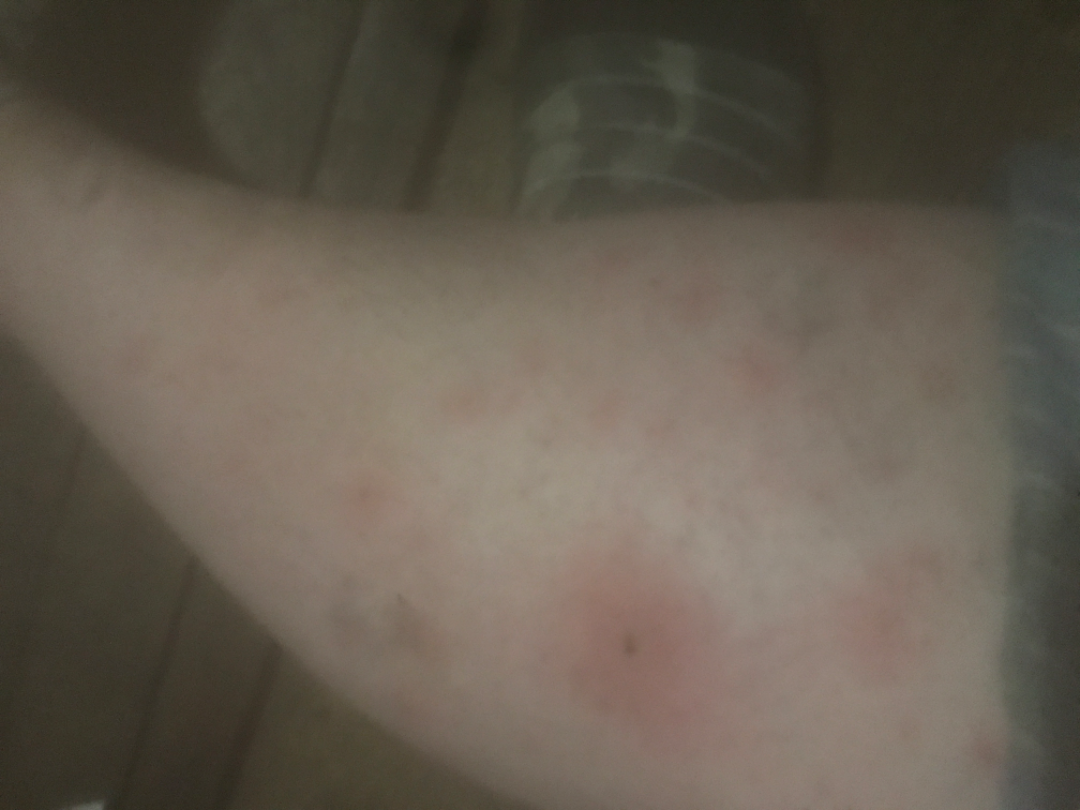{
  "assessment": "indeterminate",
  "patient_category": "a rash",
  "duration": "less than one week",
  "body_site": "leg",
  "texture": [
    "raised or bumpy",
    "fluid-filled"
  ],
  "patient": "female, age 30–39",
  "shot_type": "close-up"
}